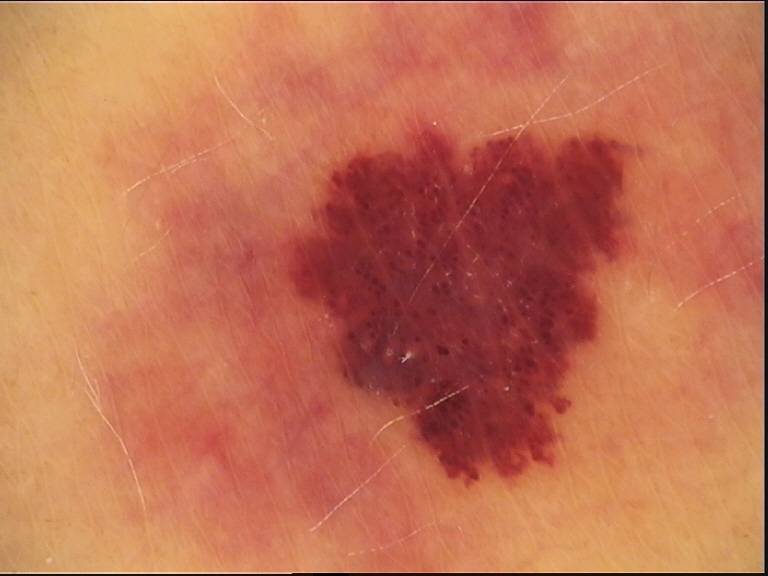diagnostic label — hemangioma (expert consensus)